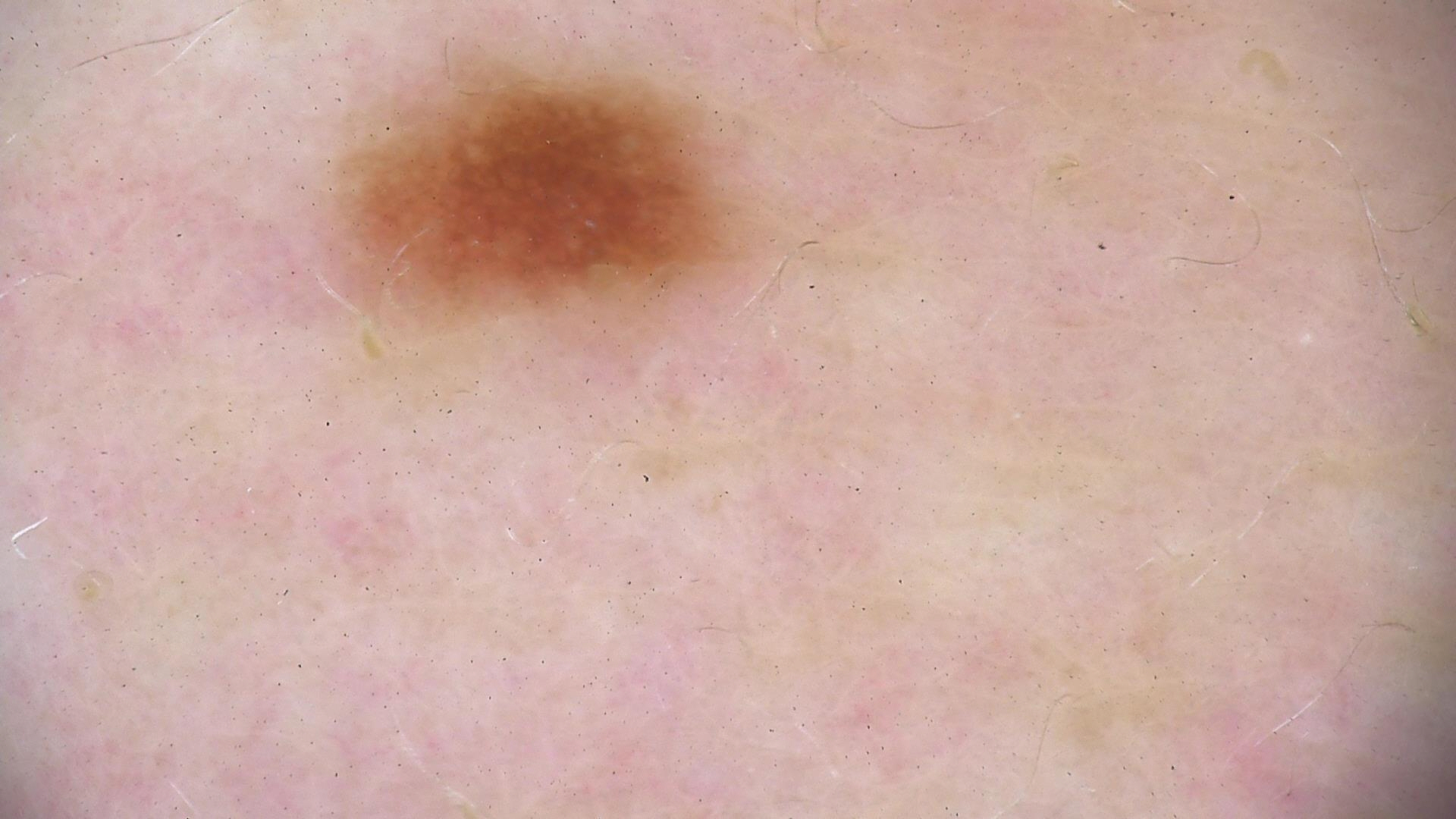Conclusion:
The diagnosis was a dysplastic junctional nevus.